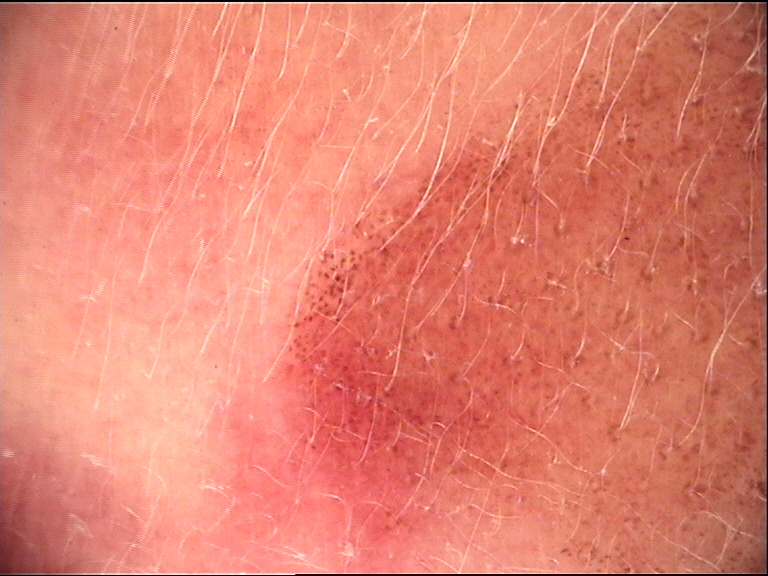The diagnosis was a congenital junctional nevus.